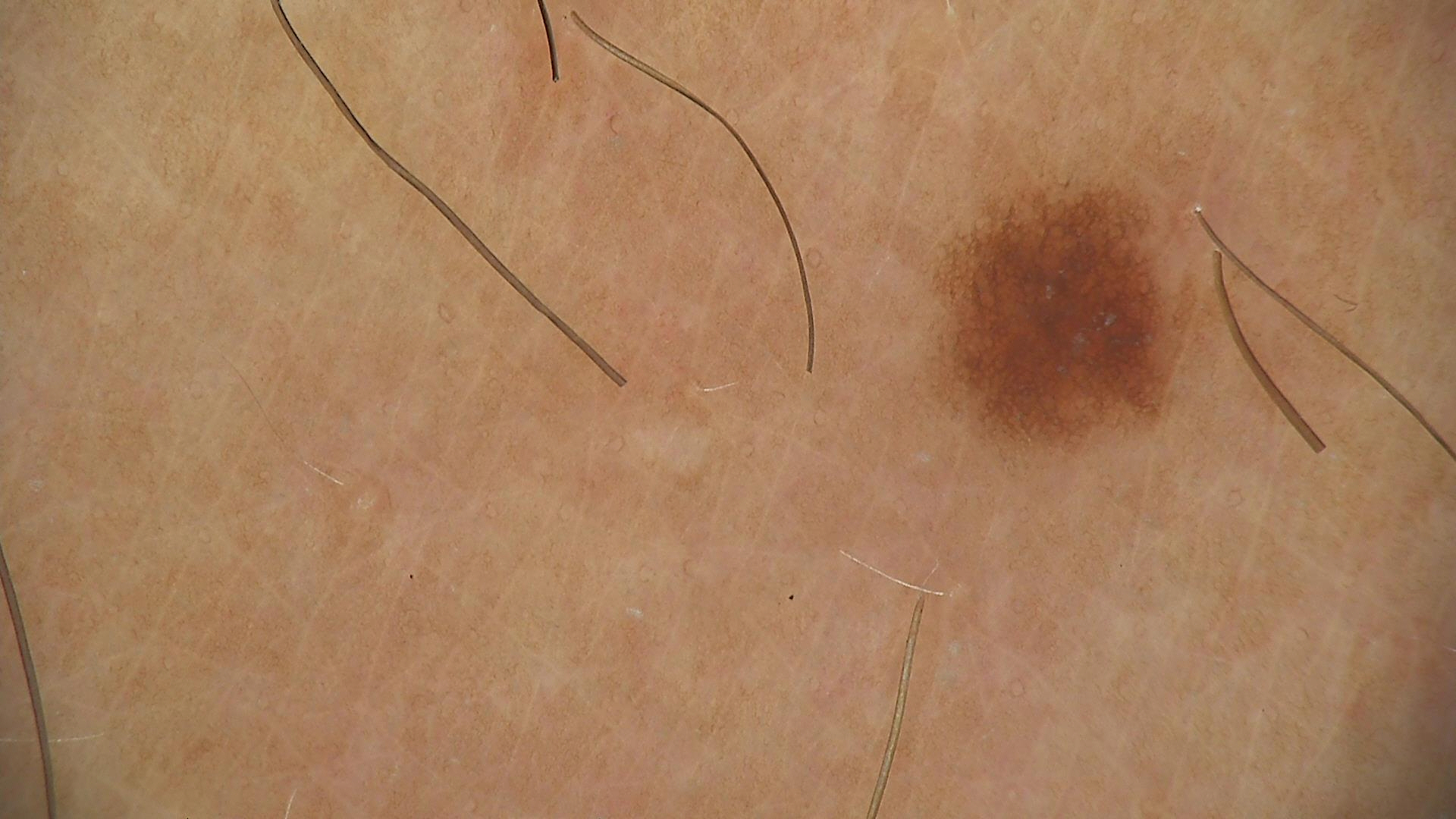diagnosis=junctional nevus (expert consensus).